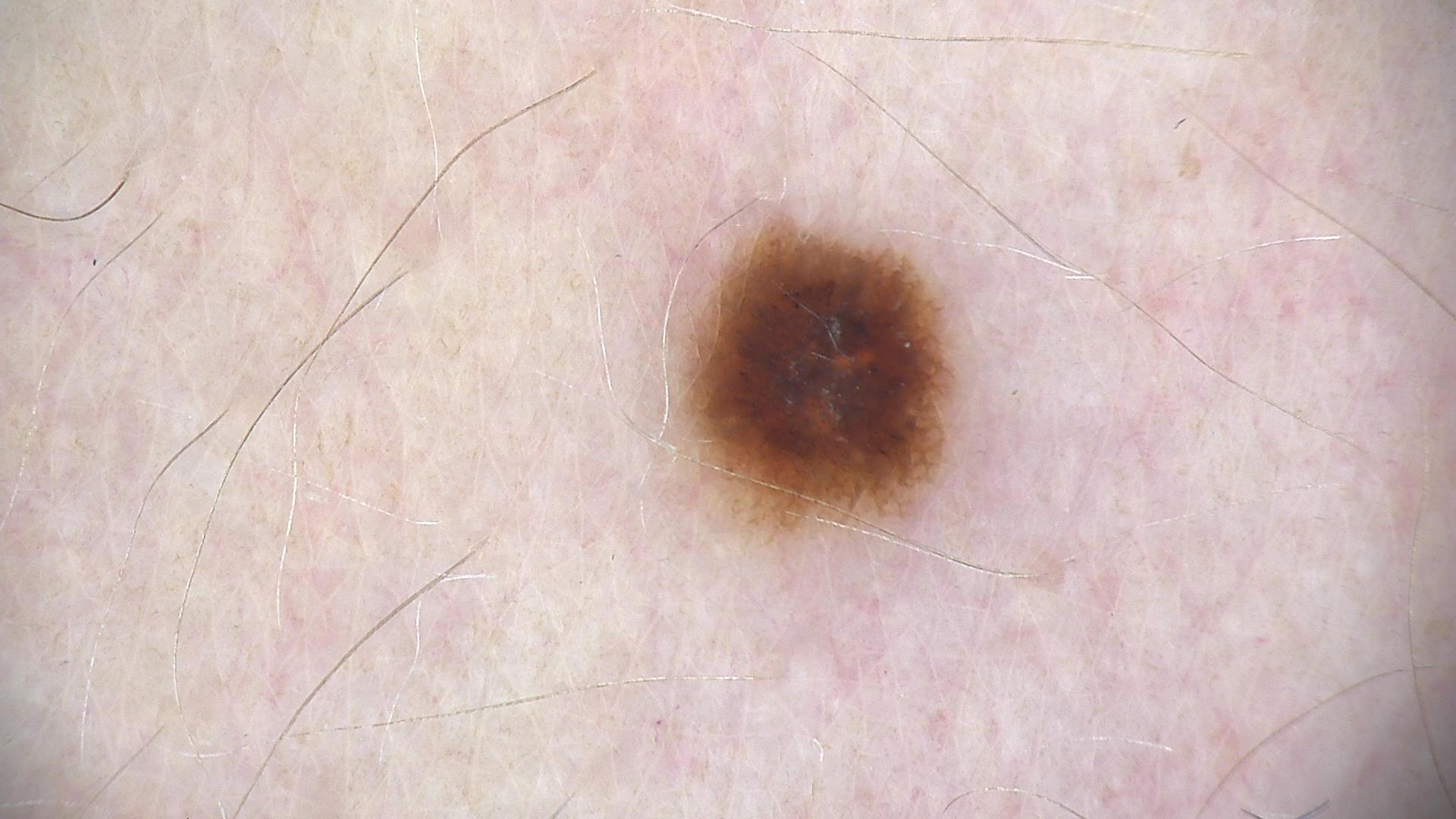A skin lesion imaged with a dermatoscope.
Labeled as a dysplastic junctional nevus.